The subject is a female aged 30–39, the patient described the issue as a rash, Fitzpatrick III, the condition has been present for one to four weeks, the photograph is a close-up of the affected area, no constitutional symptoms were reported, symptoms reported: itching, the lesion is described as rough or flaky and raised or bumpy — 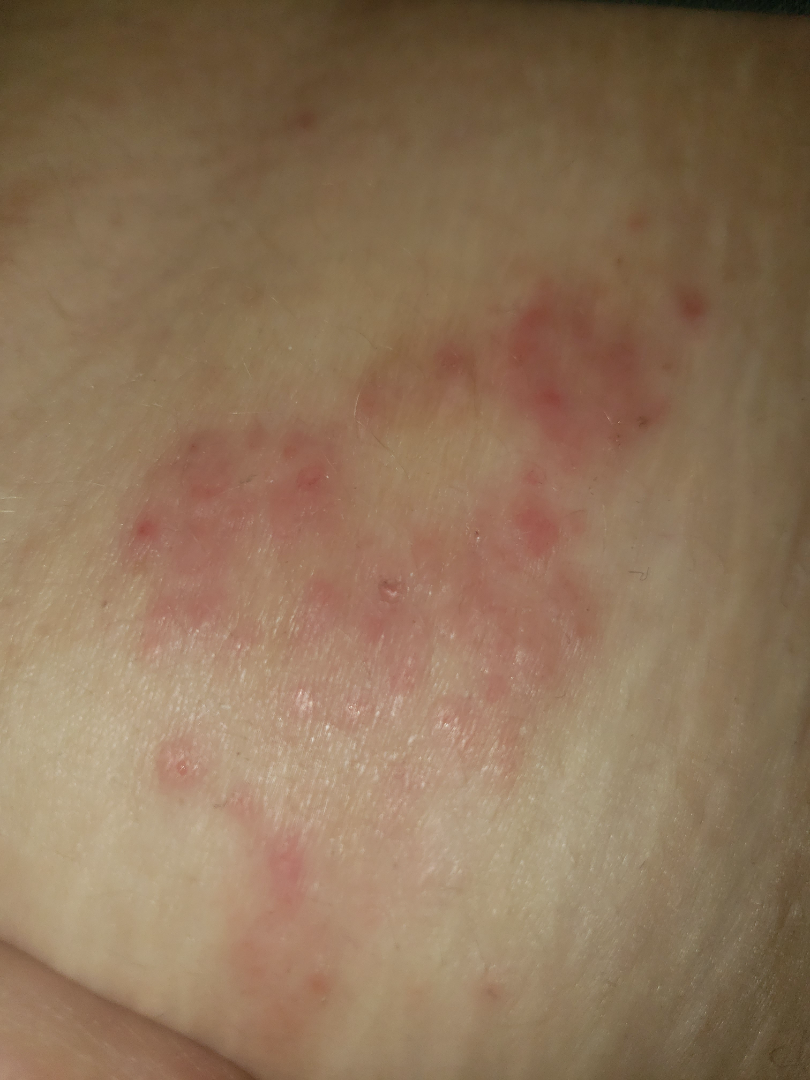differential: the leading consideration is Herpes Zoster; also consider Tinea; an alternative is Impetigo.